Female patient, age 30–39 · the patient reports the condition has been present for one to four weeks · a close-up photograph · skin tone: Fitzpatrick skin type II; lay graders estimated Monk Skin Tone 2 (US pool) or 3 (India pool) · the arm is involved · the patient considered this a rash · the patient reports itching and bothersome appearance · the lesion is described as raised or bumpy and fluid-filled — 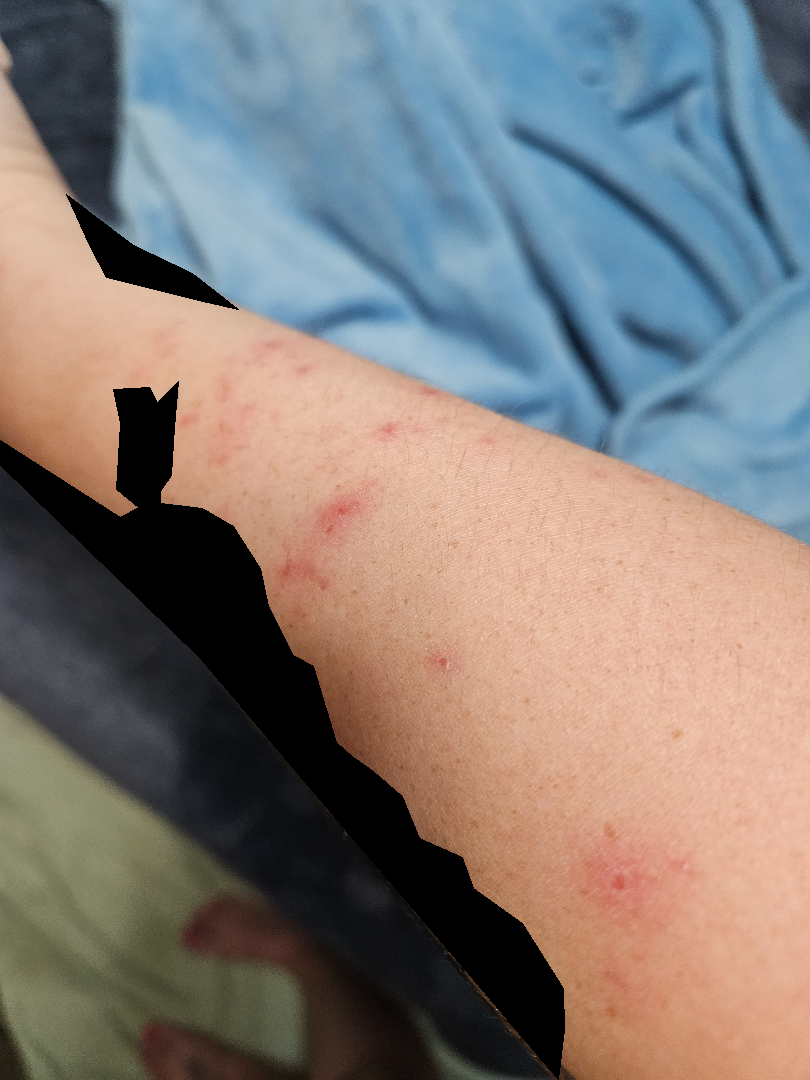The differential includes Folliculitis and Herpes Simplex, with no clear leading consideration; also consider Contact dermatitis.